A female patient 71 years of age · by history, no prior skin cancer (patient or family) · a clinical photograph showing a skin lesion · recorded as Fitzpatrick II — 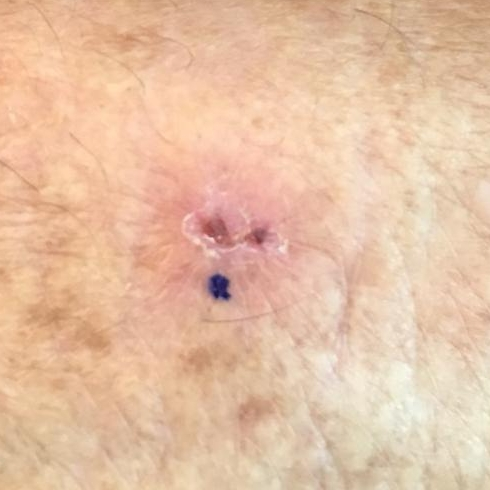Case:
– region: a forearm
– lesion size: approx. 10 × 6 mm
– diagnosis: actinic keratosis (biopsy-proven)